A male patient, aged approximately 50. A dermoscopic view of a skin lesion — 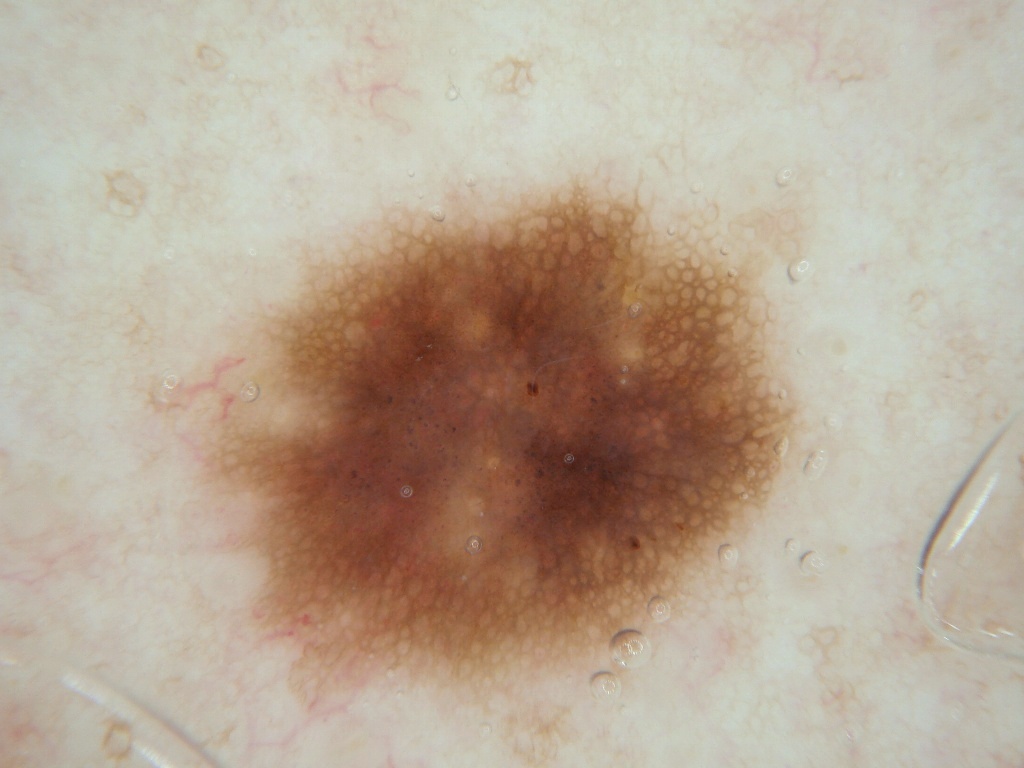Case summary:
As (left, top, right, bottom), the lesion is located at <box>154, 184, 796, 707</box>. Dermoscopic examination shows pigment network and milia-like cysts, with no globules, streaks, or negative network. The lesion takes up a moderate portion of the field.
Assessment:
Consistent with a melanocytic nevus, a benign skin lesion.